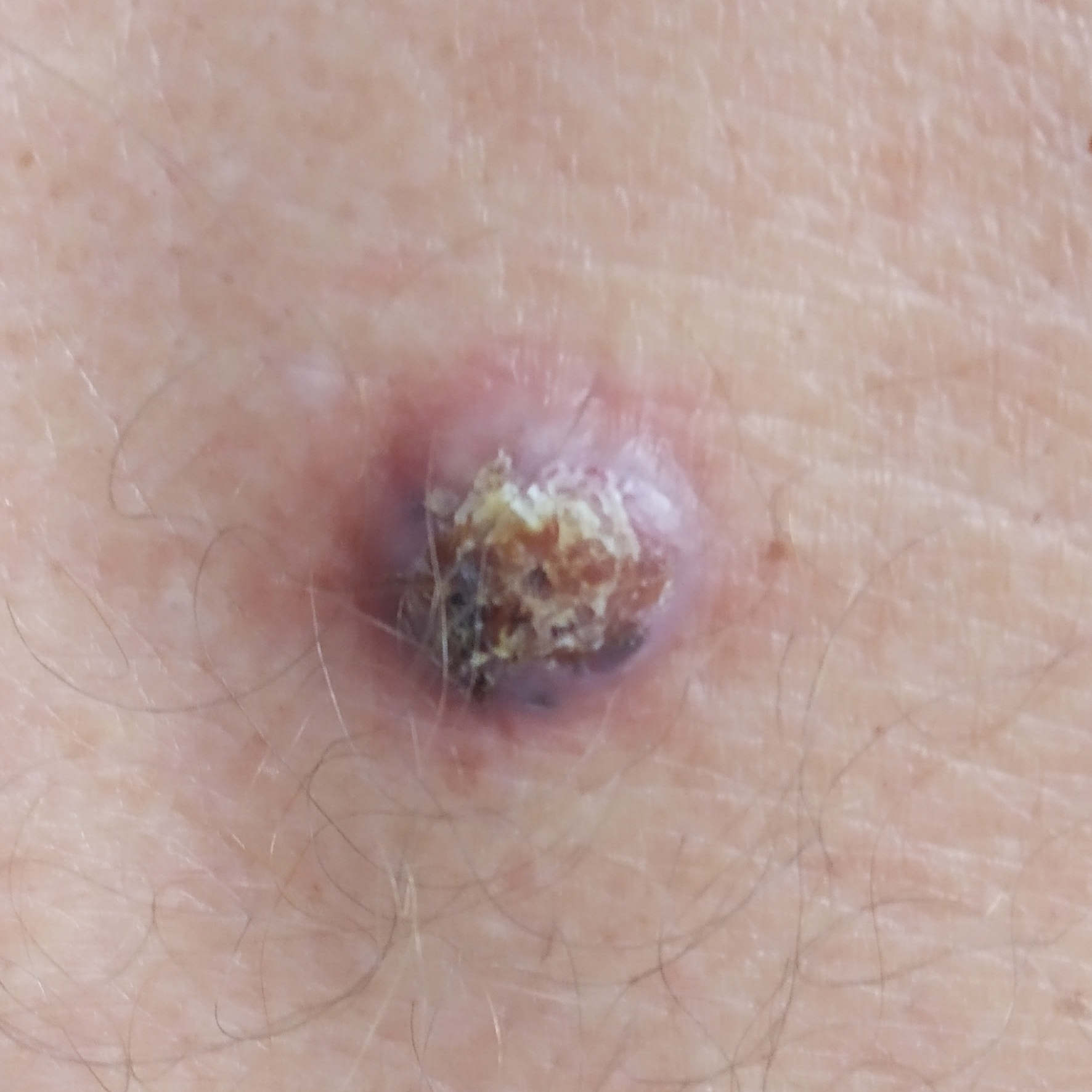A male subject in their late 60s.
The lesion was found on the back.
The patient reports that the lesion is elevated and itches.
Histopathological examination showed a basal cell carcinoma.